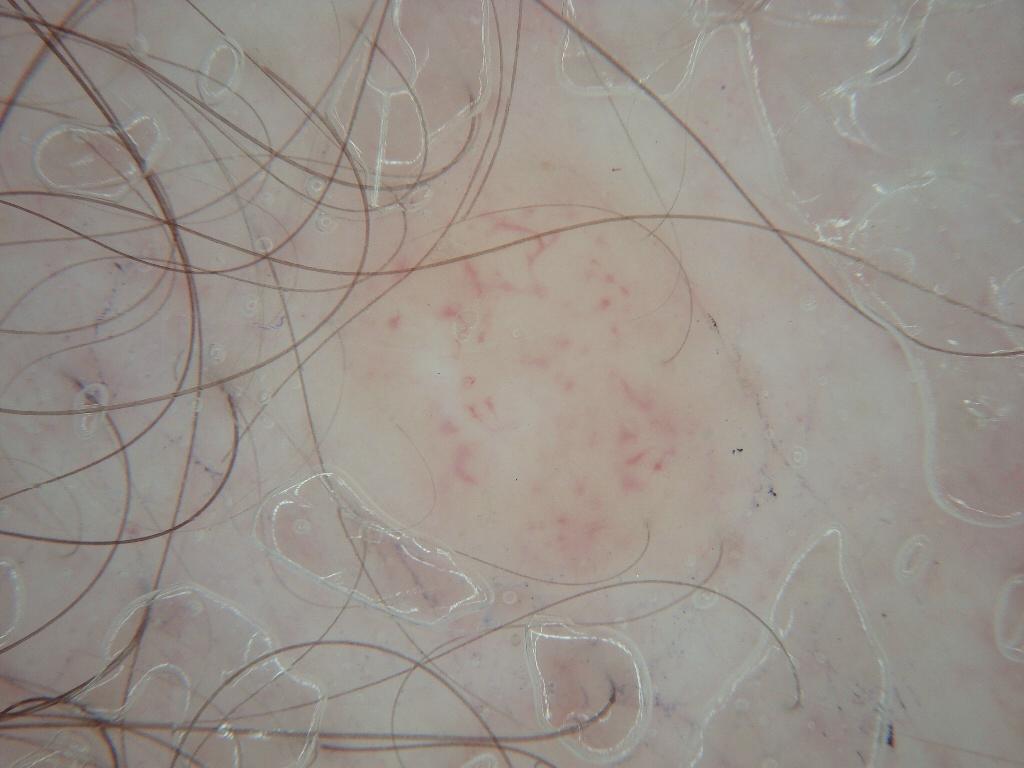<case>
  <image>
    <modality>dermoscopy</modality>
  </image>
  <lesion_location>
    <bbox_xyxy>300, 115, 780, 601</bbox_xyxy>
  </lesion_location>
  <lesion_extent>moderate</lesion_extent>
  <diagnosis>
    <malignancy>benign</malignancy>
    <provenance>clinical</provenance>
  </diagnosis>
</case>